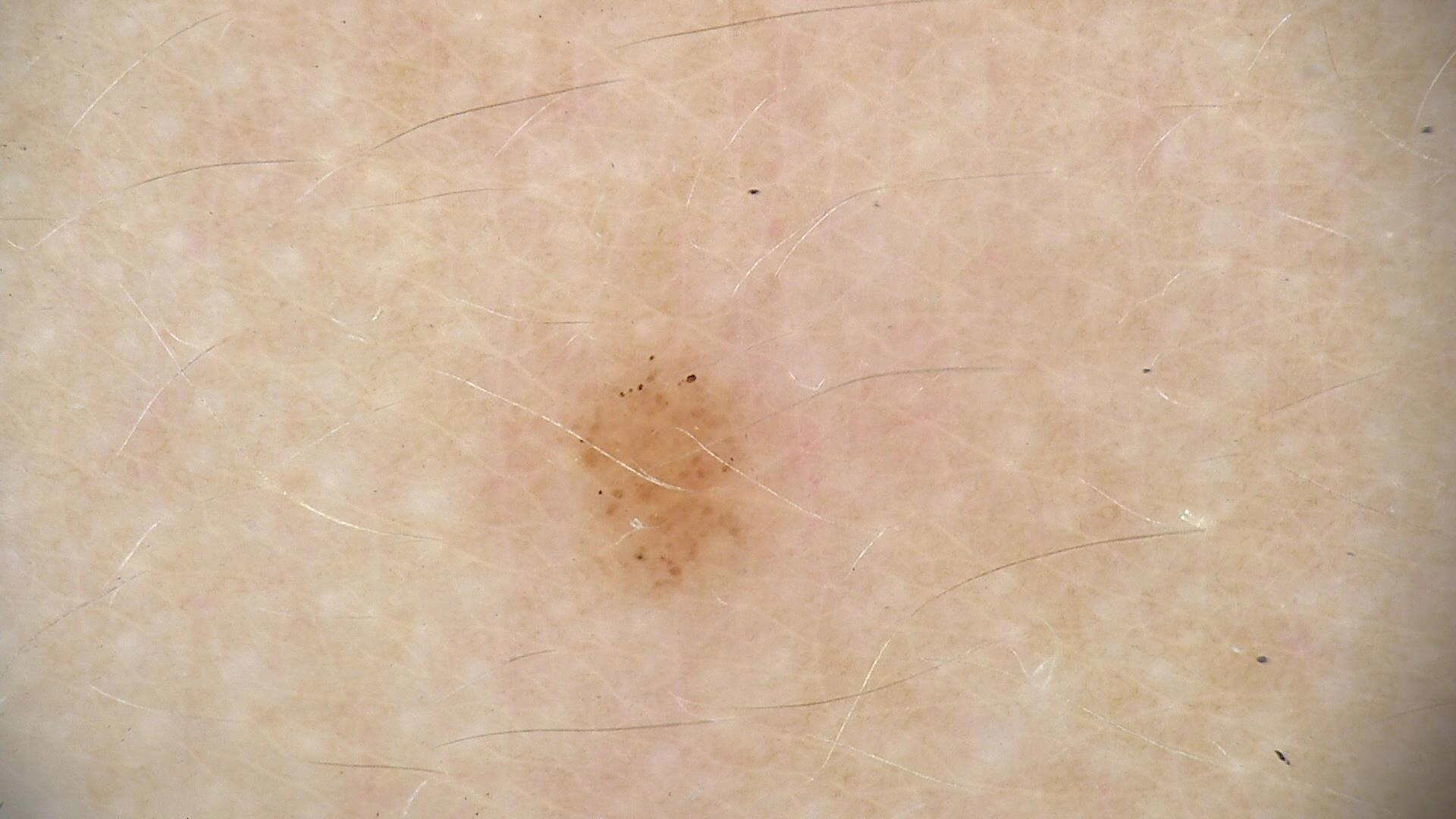<dermoscopy>
  <image>dermatoscopy</image>
  <diagnosis>
    <name>dysplastic junctional nevus</name>
    <code>jd</code>
    <malignancy>benign</malignancy>
    <super_class>melanocytic</super_class>
    <confirmation>expert consensus</confirmation>
  </diagnosis>
</dermoscopy>